The patient is Fitzpatrick I · a female patient approximately 65 years of age · contact-polarized dermoscopy of a skin lesion — 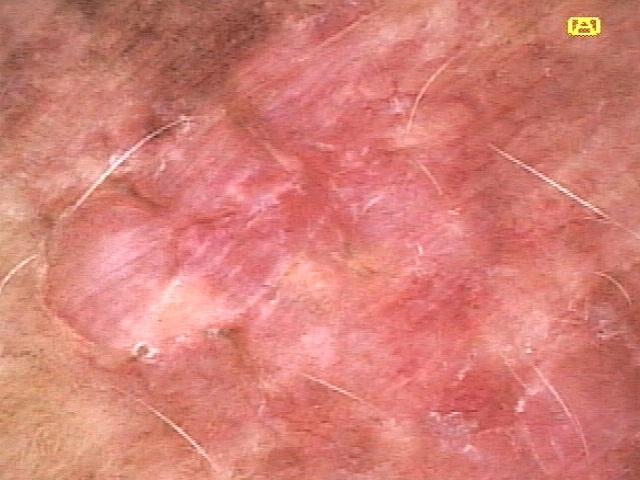Notes:
– pathology · Solar or actinic keratosis (biopsy-proven)